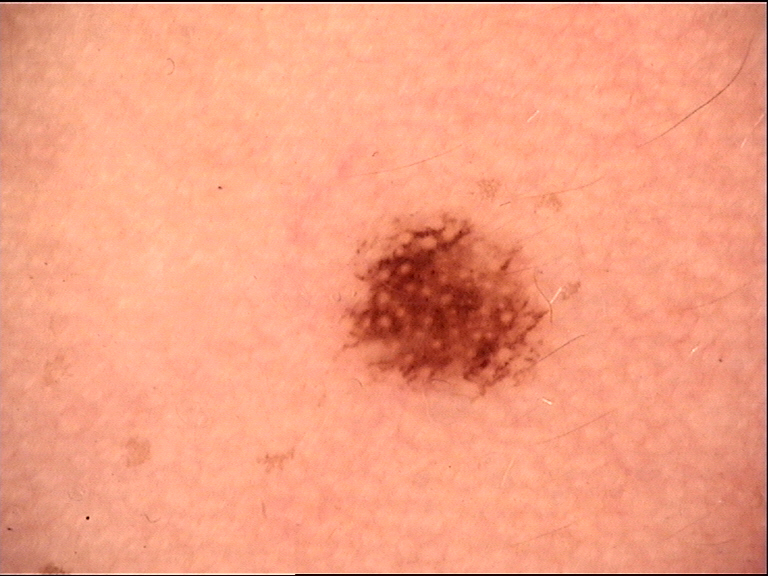Consistent with a banal lesion — a Miescher nevus.